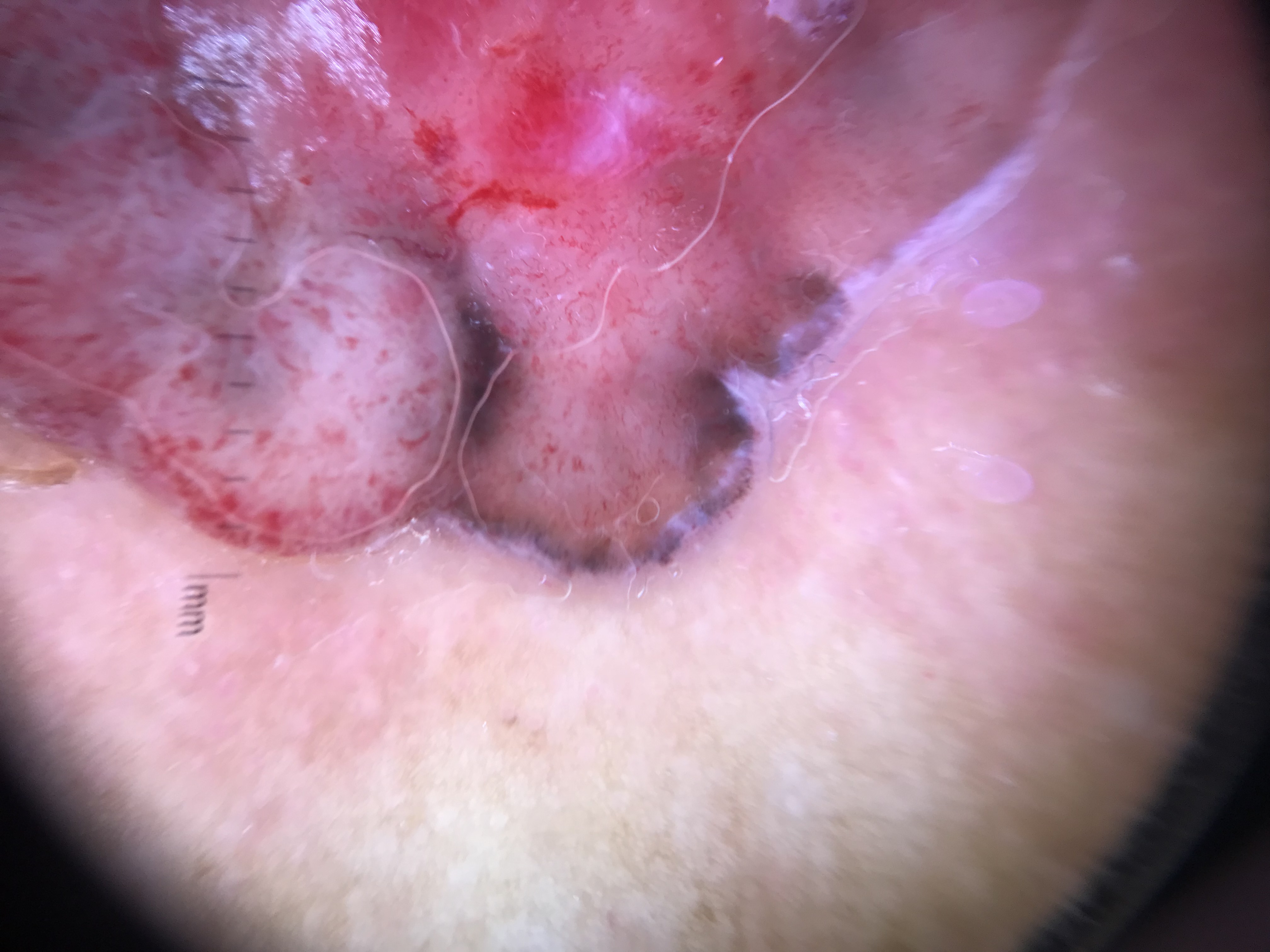Dermoscopy of a skin lesion. The biopsy diagnosis was a malignant lesion — a basal cell carcinoma.